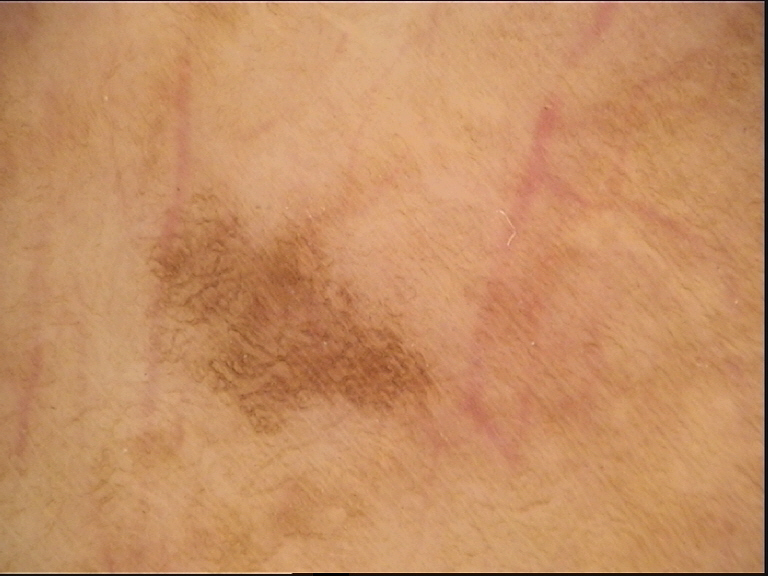Q: What was the diagnostic impression?
A: solar lentigo (expert consensus)